Close-up view; located on the arm, back of the torso and leg; the patient is 30–39, male.
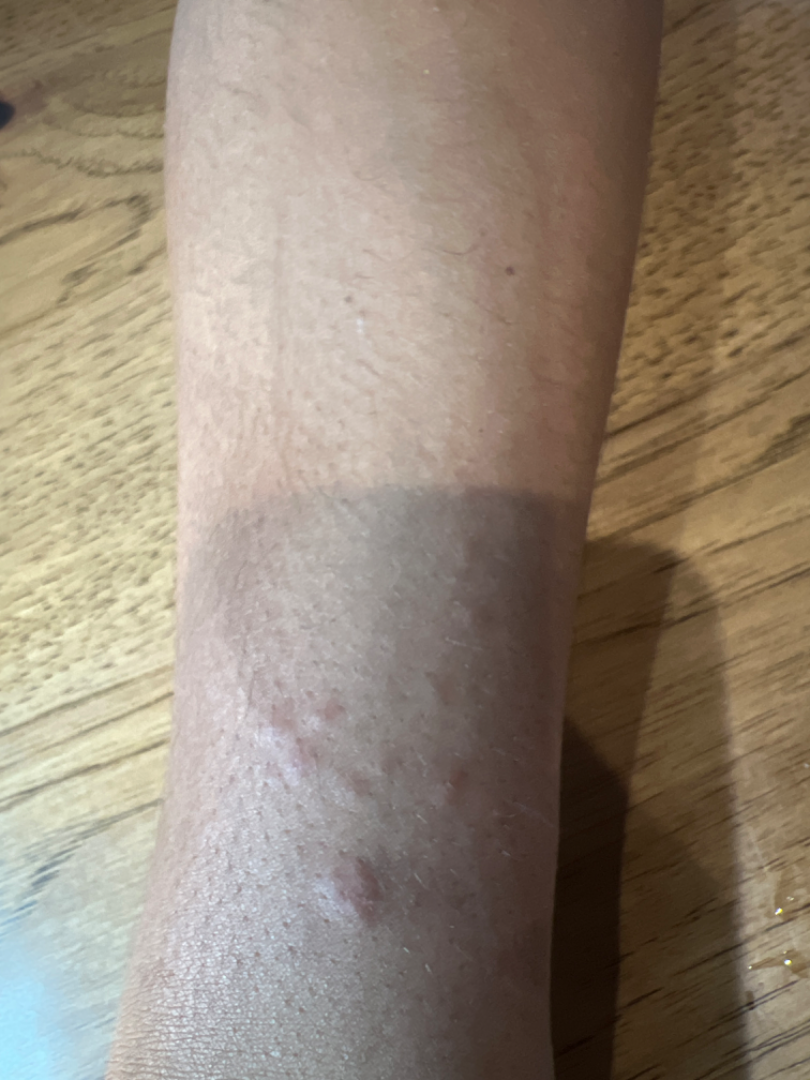The case was difficult to assess from the available photograph. The patient reported no systemic symptoms. The lesion is described as raised or bumpy. The patient described the issue as a rash. Reported lesion symptoms include itching.